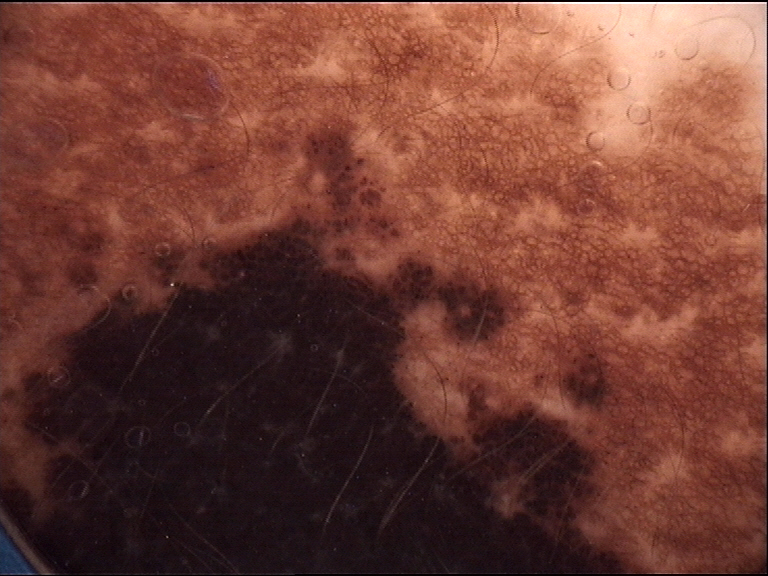diagnostic label: congenital compound nevus (expert consensus)